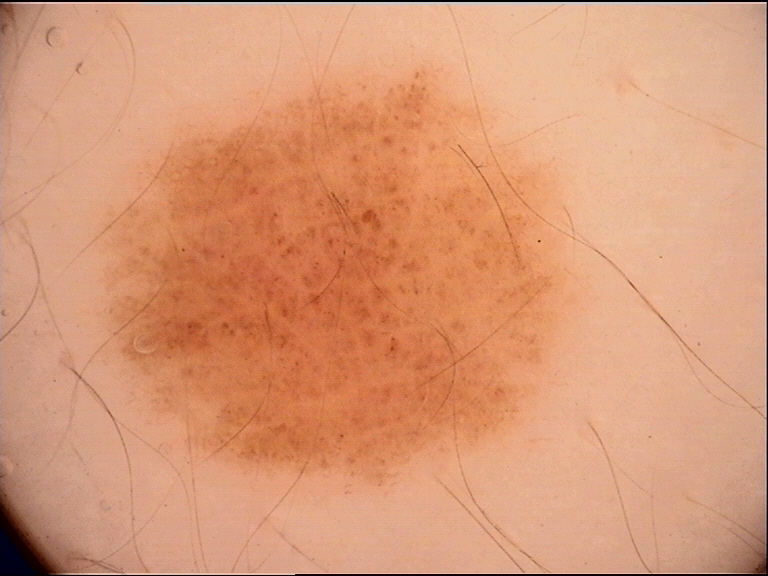A dermoscopic photograph of a skin lesion.
The architecture is that of a banal lesion.
The diagnostic label was a junctional nevus.